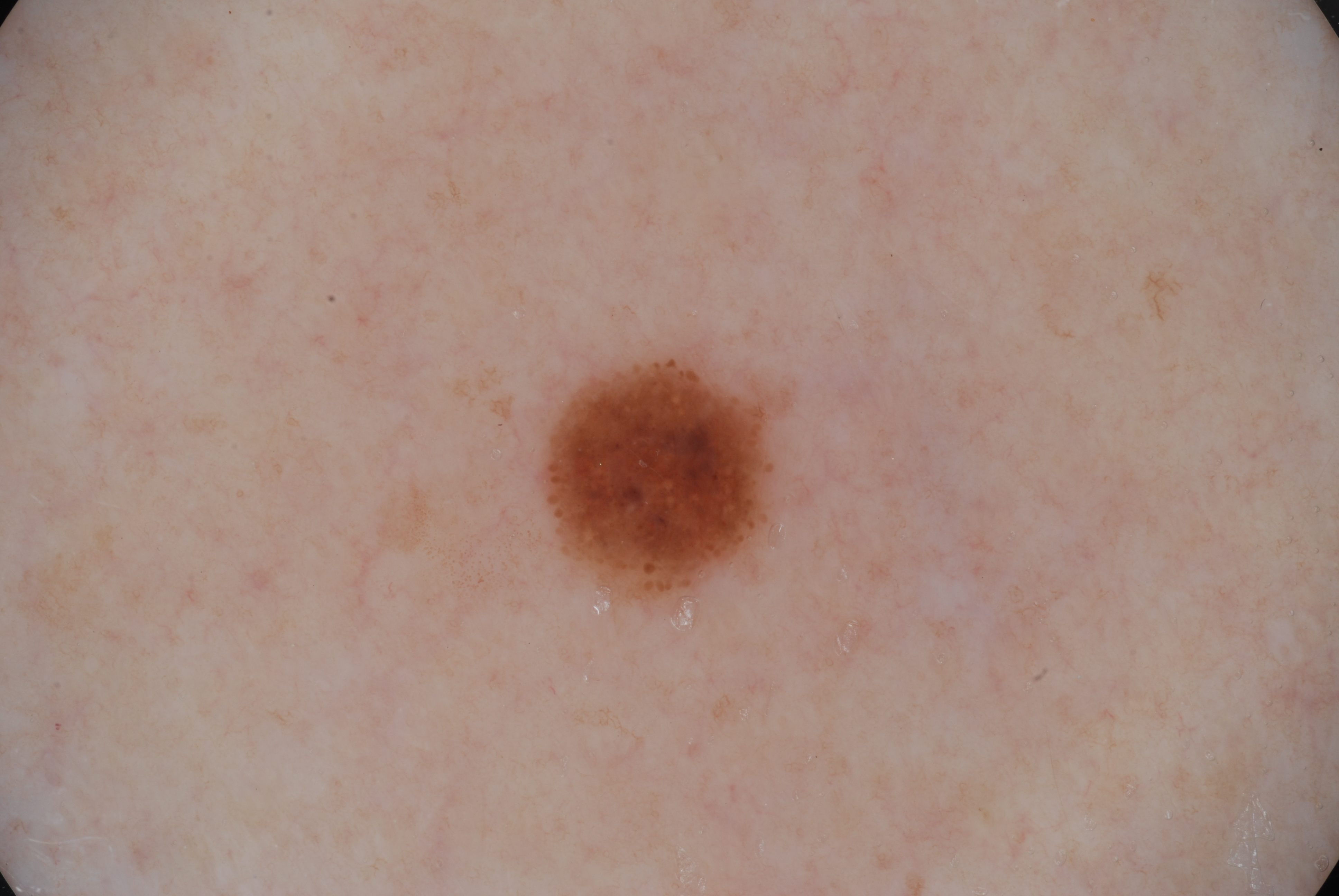Q: Who is the patient?
A: female, aged 33 to 37
Q: What kind of image is this?
A: dermoscopy of a skin lesion
Q: Where is the lesion located?
A: [539, 357, 776, 603]
Q: Which dermoscopic features were noted?
A: pigment network
Q: Lesion extent?
A: ~4% of the field
Q: What is this lesion?
A: a melanocytic nevus, a benign lesion